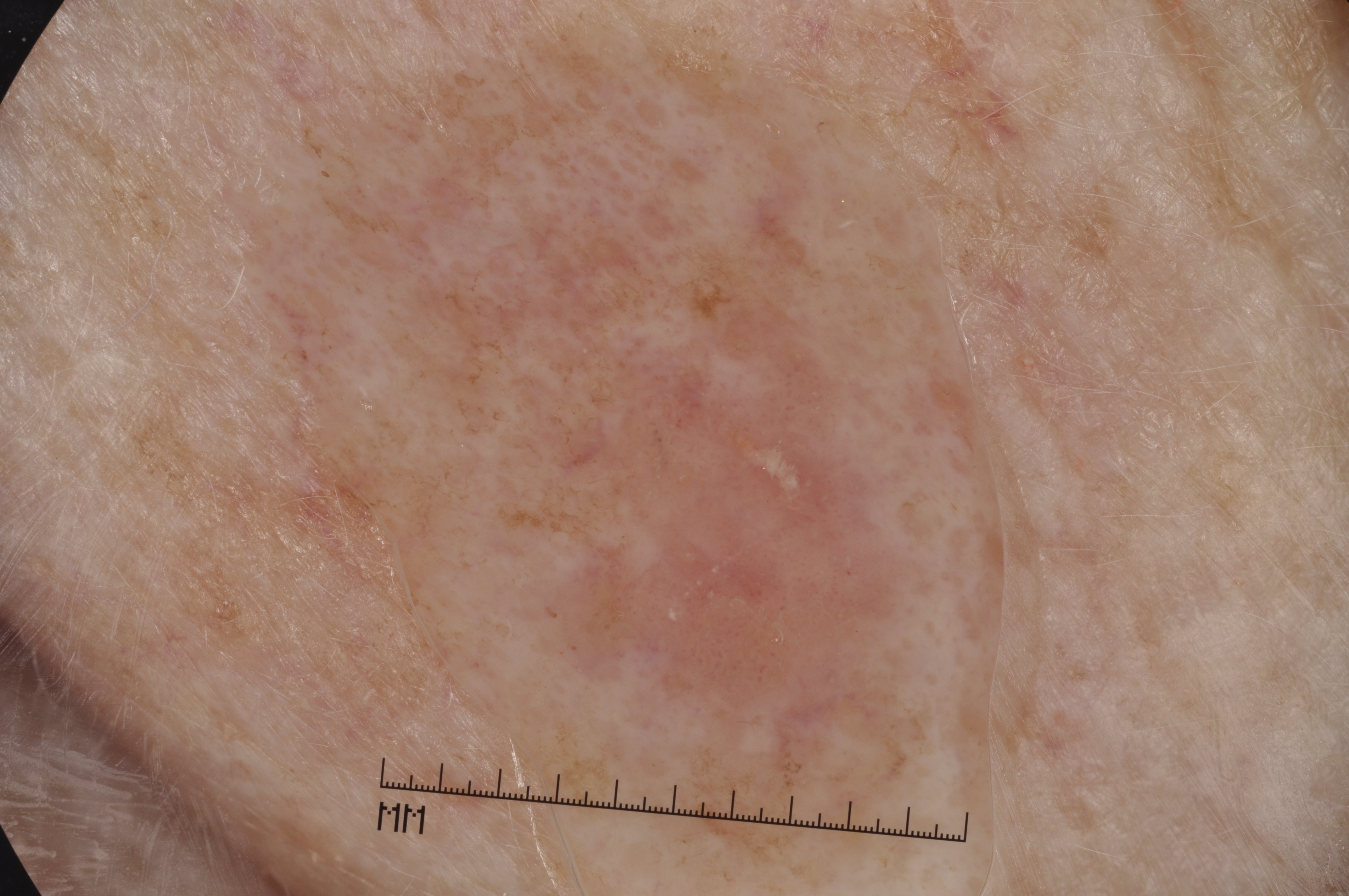<record>
  <image>
    <modality>dermoscopy</modality>
  </image>
  <lesion_extent>large</lesion_extent>
  <dermoscopic_features>
    <present/>
    <absent>milia-like cysts, streaks, negative network, pigment network</absent>
  </dermoscopic_features>
  <lesion_location>
    <bbox_xyxy>272, 56, 1034, 892</bbox_xyxy>
  </lesion_location>
  <diagnosis>
    <name>seborrheic keratosis</name>
    <malignancy>benign</malignancy>
    <lineage>keratinocytic</lineage>
    <provenance>clinical</provenance>
  </diagnosis>
</record>